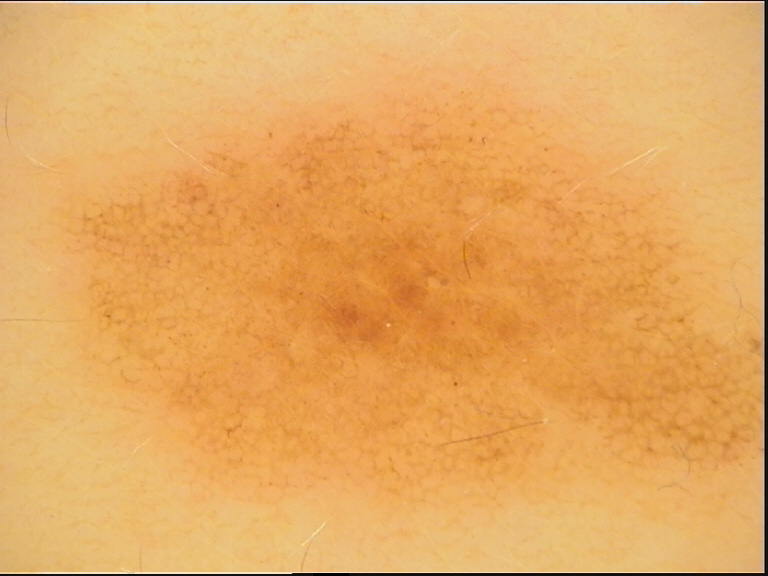A dermoscopy image of a single skin lesion.
The architecture is that of a banal lesion.
The diagnostic label was a junctional nevus.